No constitutional symptoms were reported; the patient described the issue as a rash; the contributor notes the condition has been present for more than five years; an image taken at an angle; the sole of the foot is involved; the lesion is associated with enlargement and bothersome appearance — 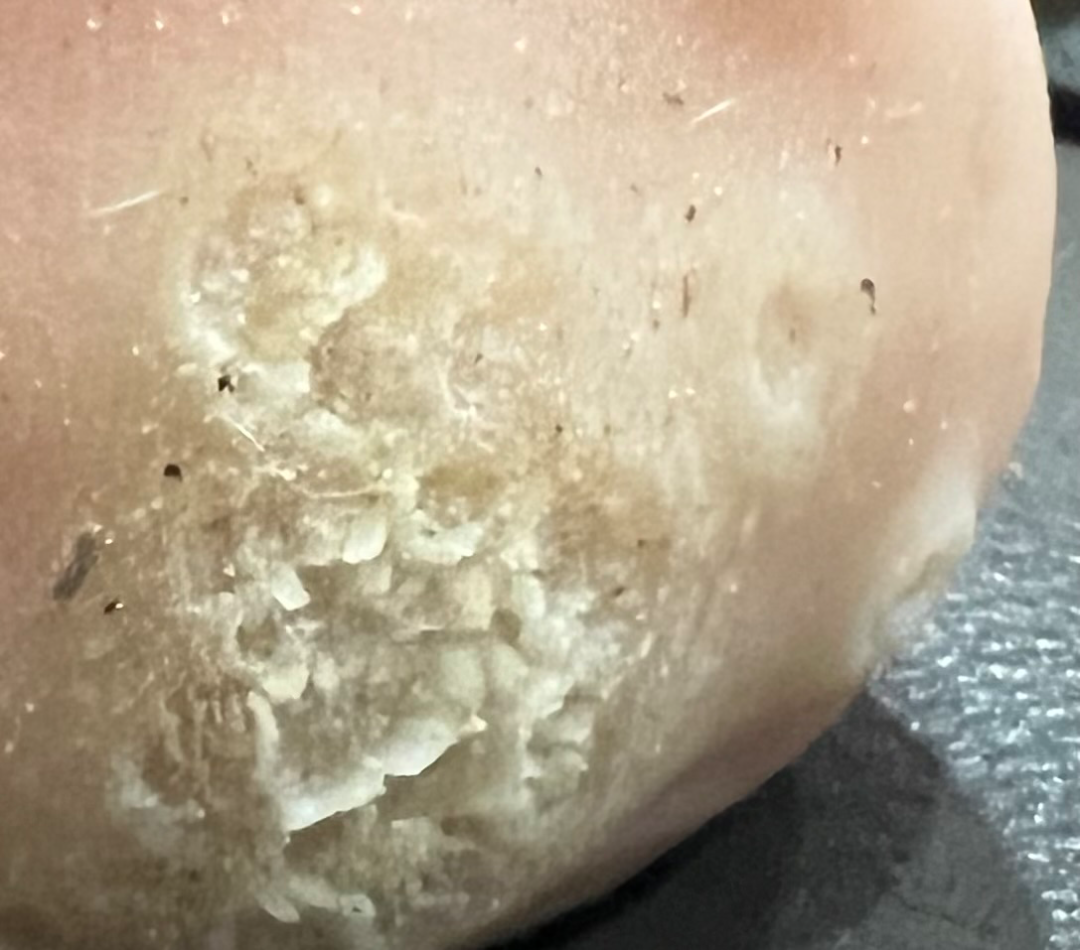Review:
The reviewing clinician's impression was: most consistent with Verruca vulgaris.